A patient 20 years of age. A clinical photograph of a skin lesion: 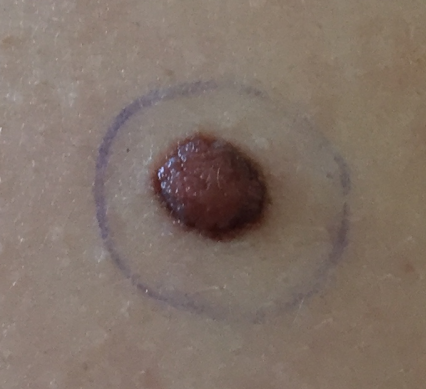Located on the back. The patient describes that the lesion is elevated, but has not grown and has not changed. Consistent with a benign skin lesion — a nevus.